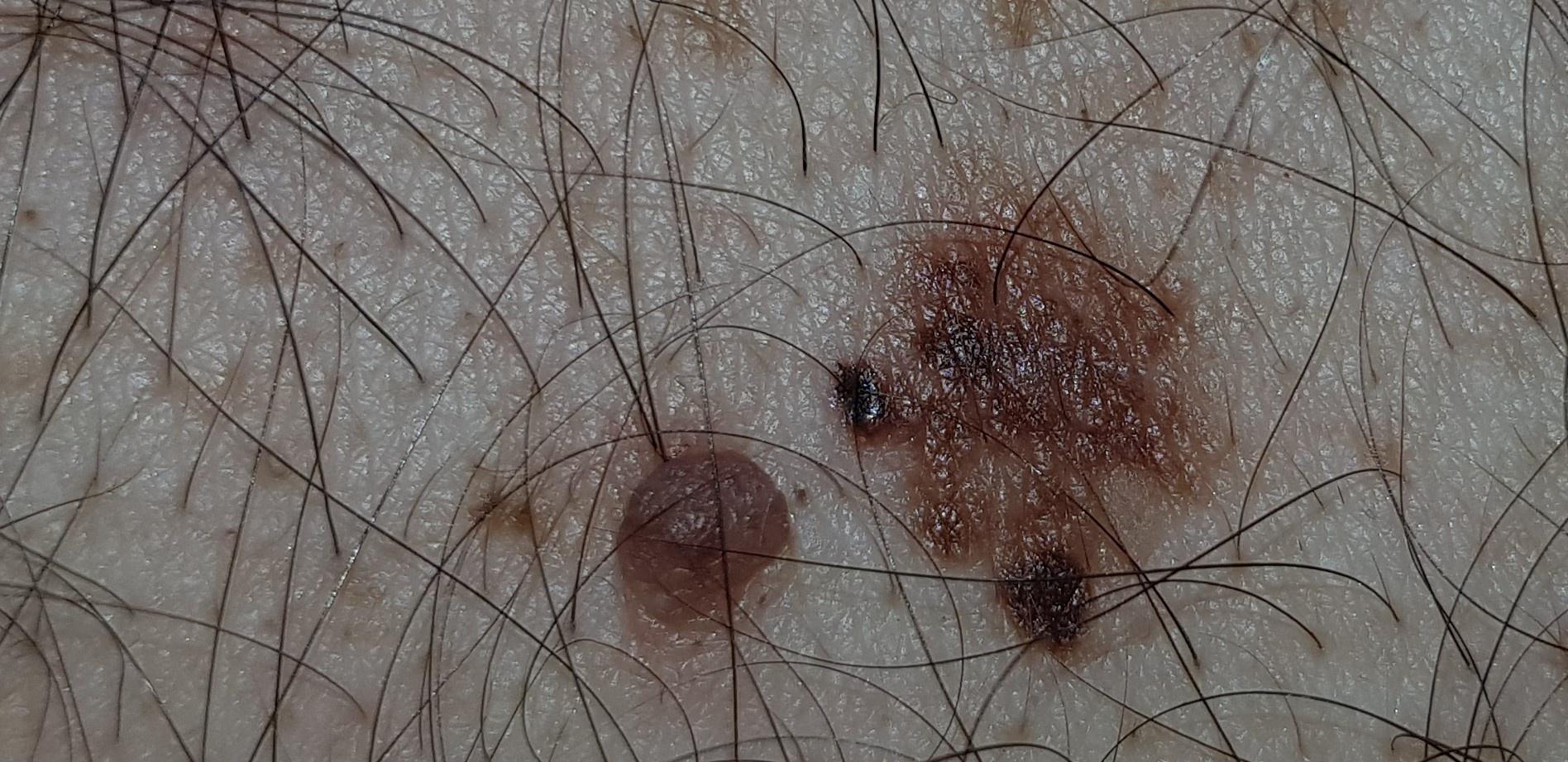  skin_type: II
  image: clinical photograph
  patient:
    age_approx: 60
    sex: male
  lesion_location:
    region: the trunk
    detail: the posterior trunk
  diagnosis:
    name: Melanoma
    malignancy: malignant
    confirmation: histopathology